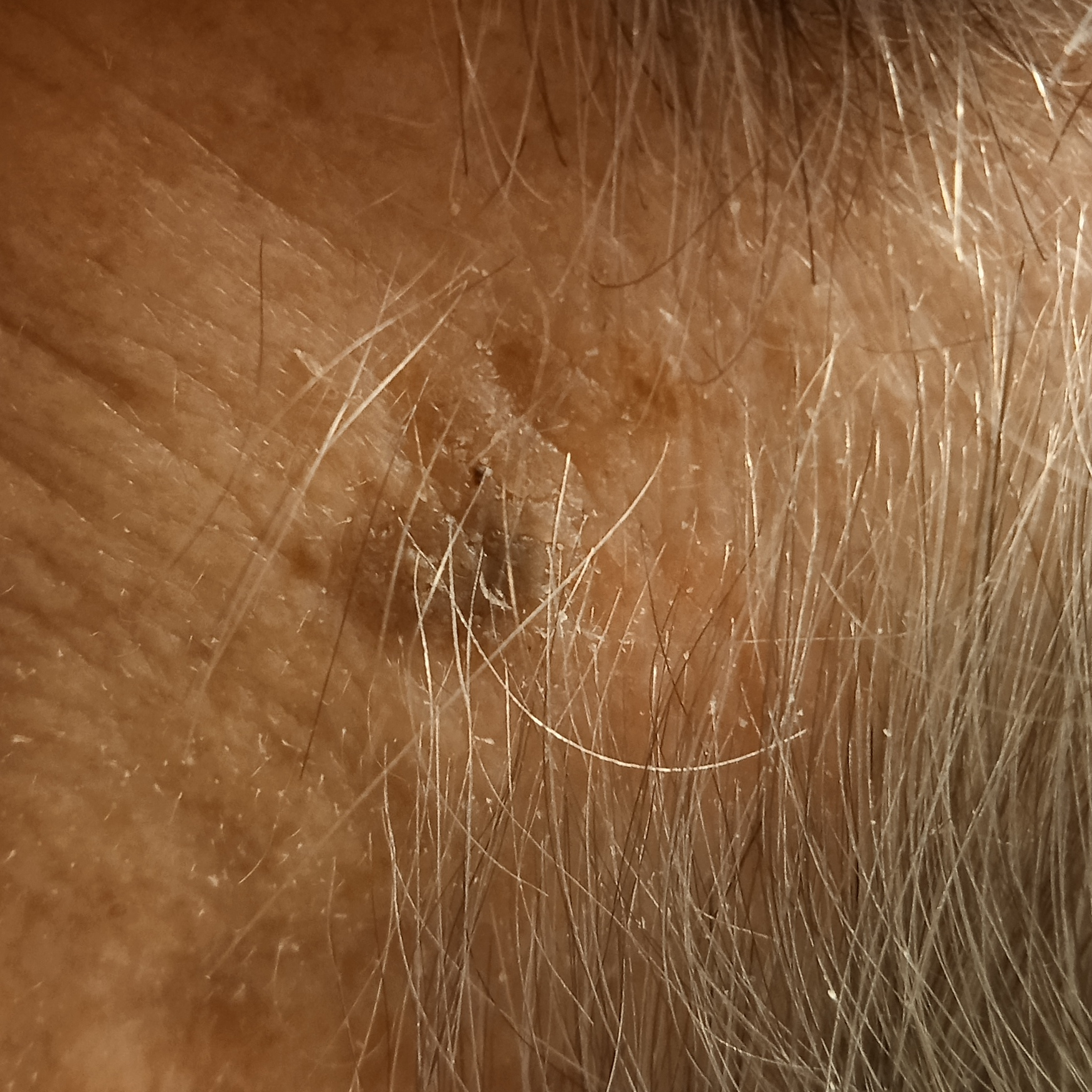Conclusion: The consensus diagnosis for this lesion was a seborrheic keratosis.